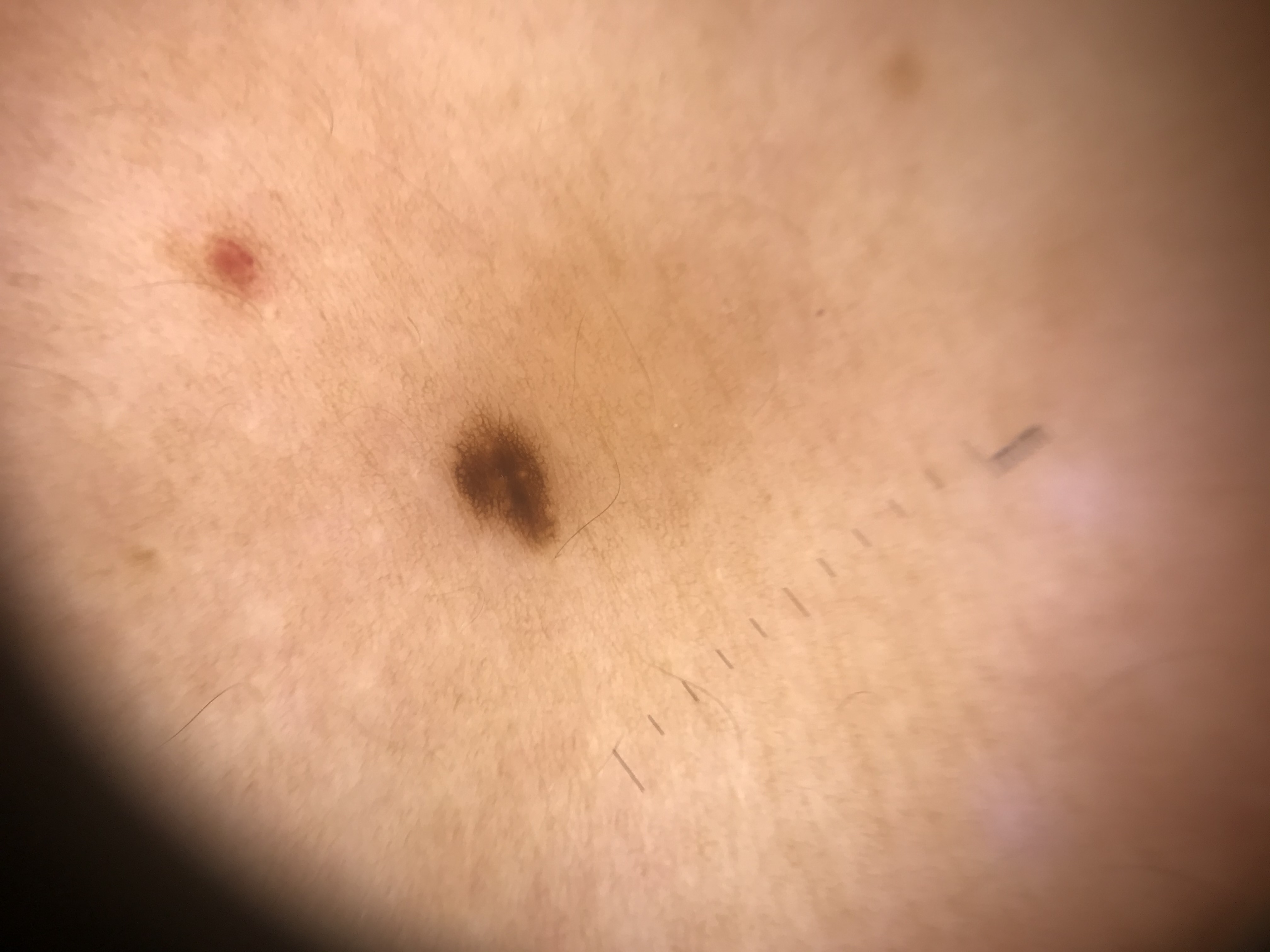modality = dermatoscopy; category = banal; diagnosis = junctional nevus (expert consensus).